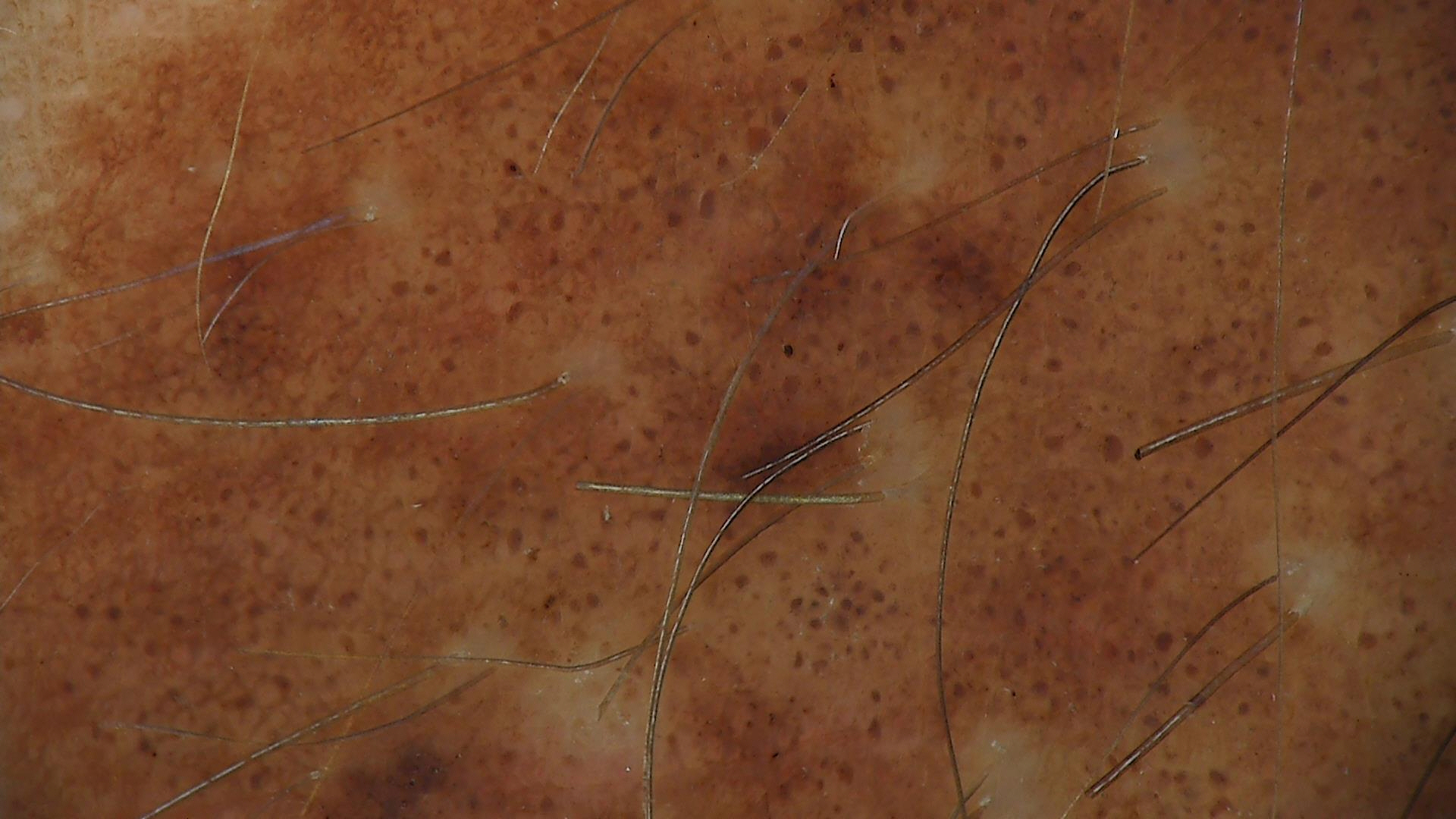Labeled as a banal lesion — a congenital junctional nevus.